A dermoscopic close-up of a skin lesion.
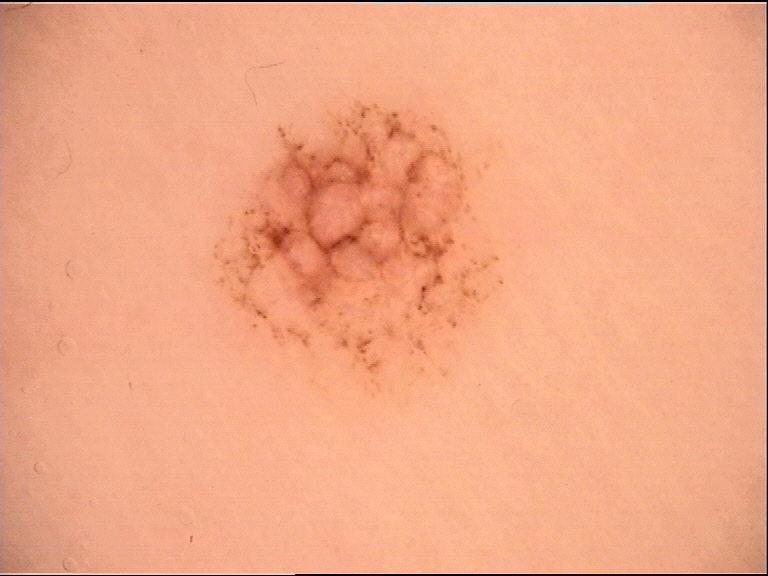Labeled as a benign lesion — an acral dysplastic junctional nevus.